Located on the sole of the foot. The patient is a female aged 30–39. The photograph is a close-up of the affected area — 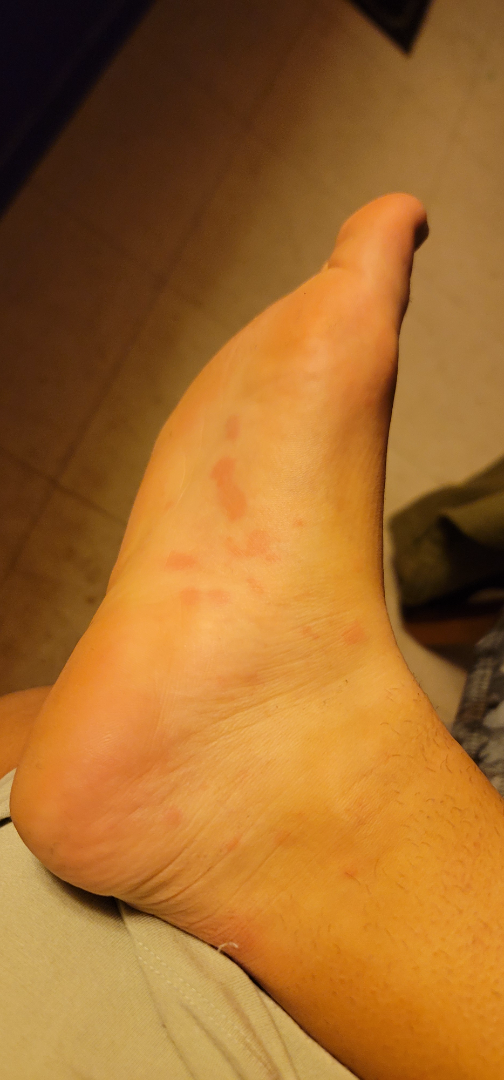The reviewing dermatologist's impression was: Viral Exanthem, Erythema multiforme and Syphilis were considered with similar weight.